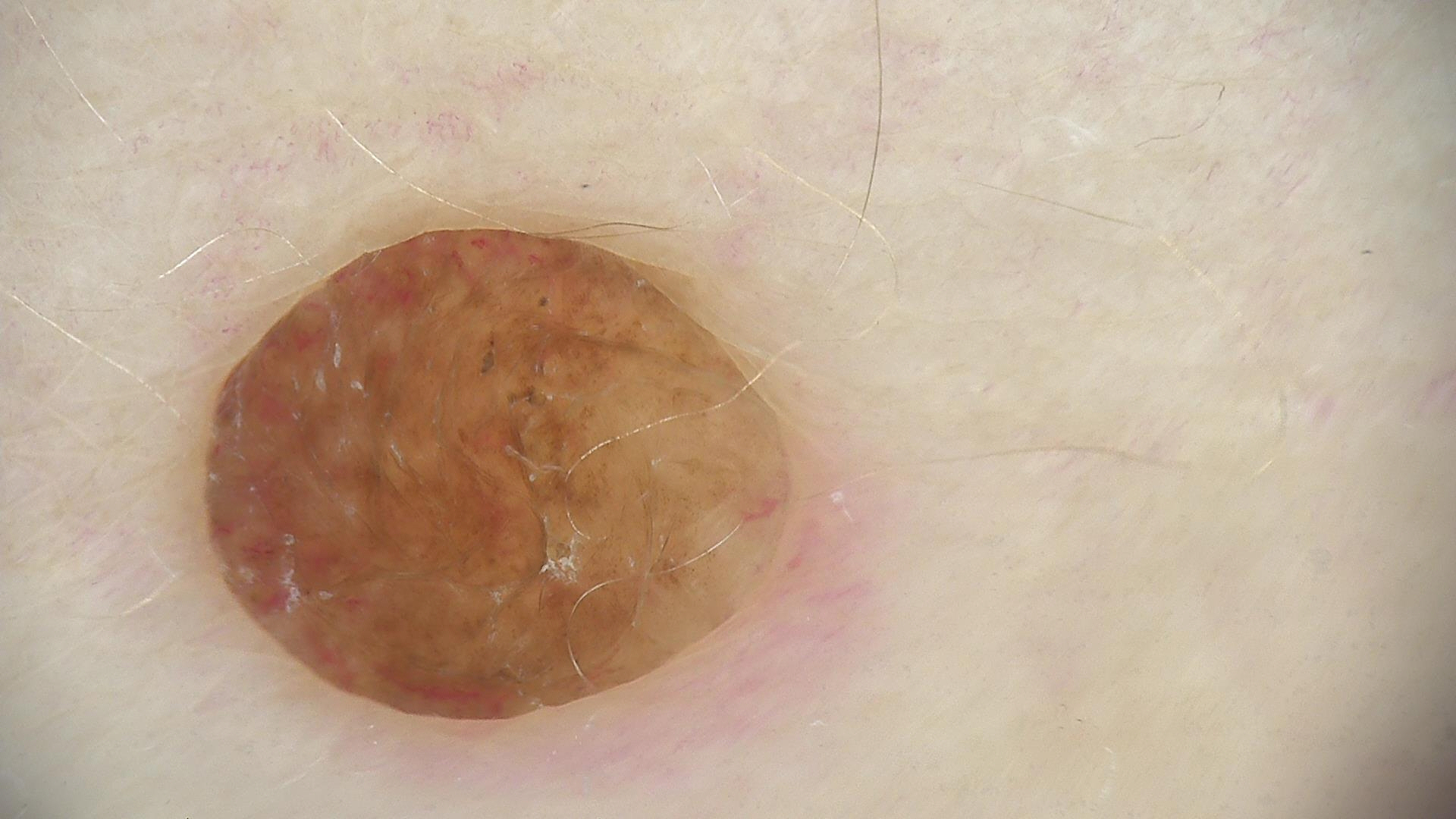assessment: dermal nevus (expert consensus).